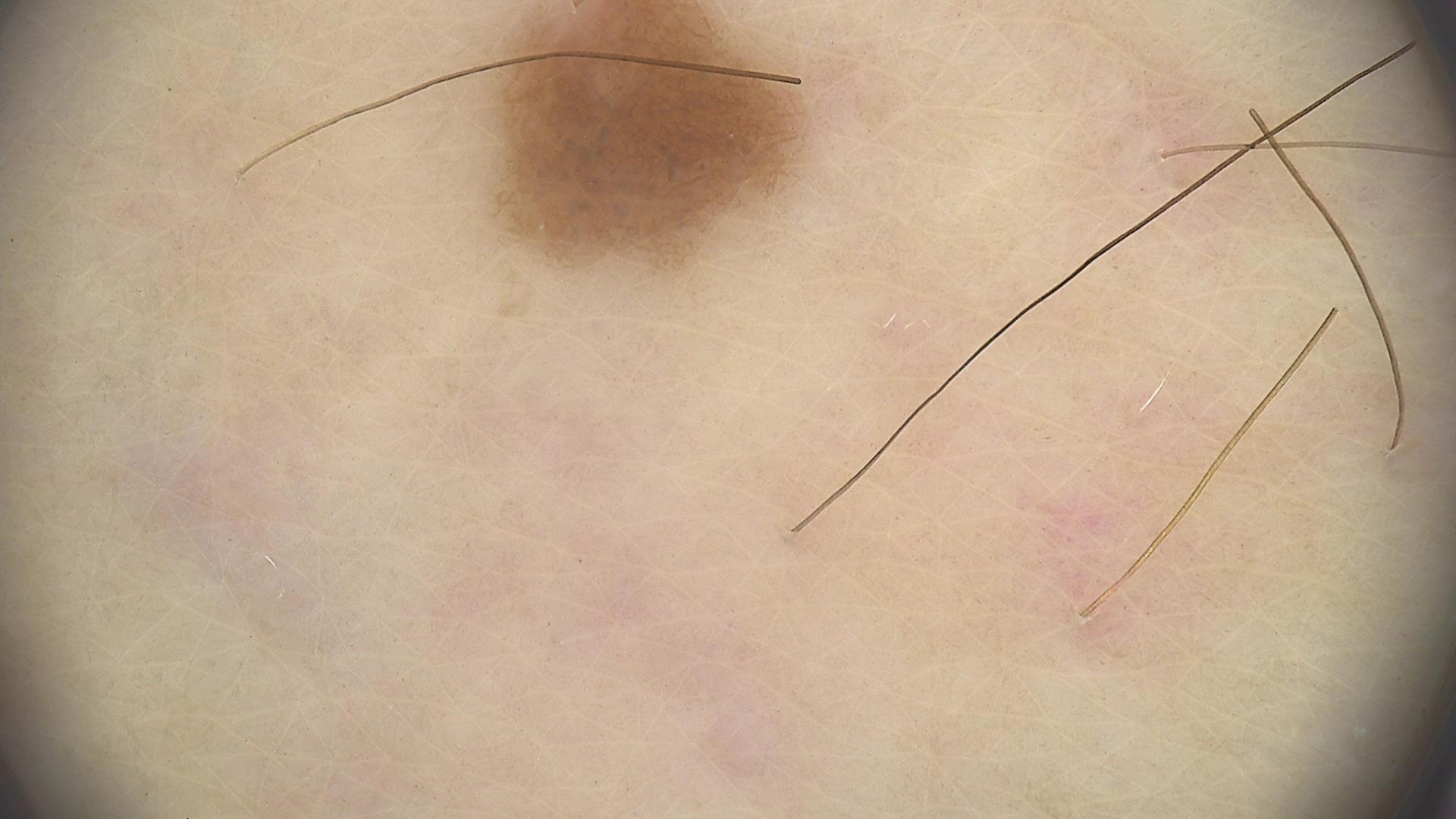{"diagnosis": {"name": "dysplastic junctional nevus", "code": "jd", "malignancy": "benign", "super_class": "melanocytic", "confirmation": "expert consensus"}}